A dermoscopic photograph of a skin lesion: 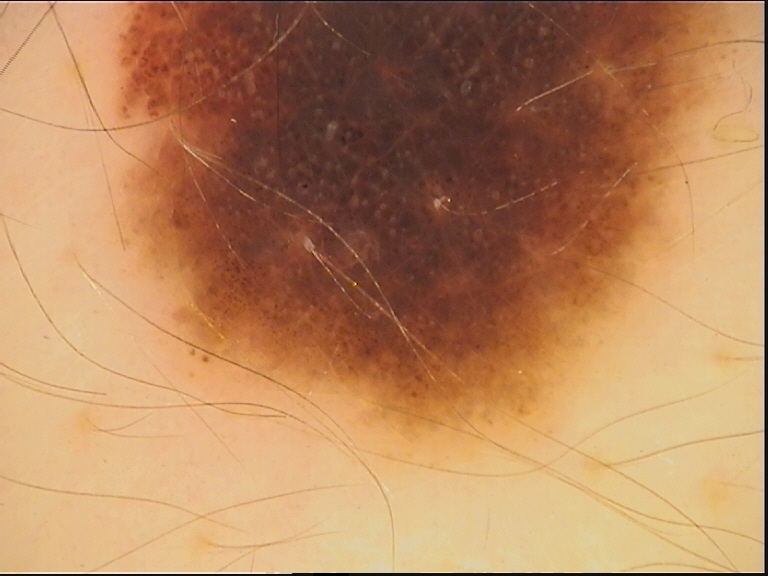Consistent with a banal lesion — a congenital compound nevus.